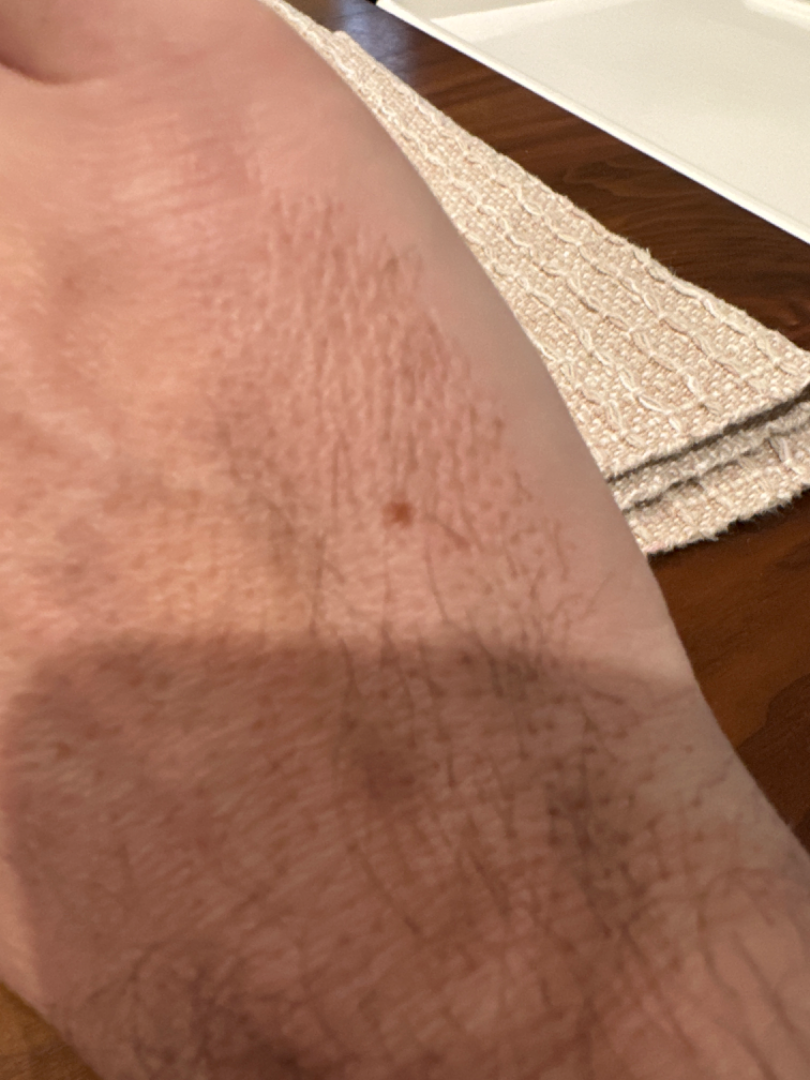History: The subject is 40–49, male. The patient reported no systemic symptoms. The affected area is the back of the hand. The patient indicates the lesion is flat. The patient did not report lesion symptoms. A close-up photograph. FST II; human graders estimated MST 3 (US pool) or 4 (India pool). The patient indicates the condition has been present for since childhood. Impression: A single dermatologist reviewed the case: the differential is split between Melanocytic Nevus and Atypical Nevus.